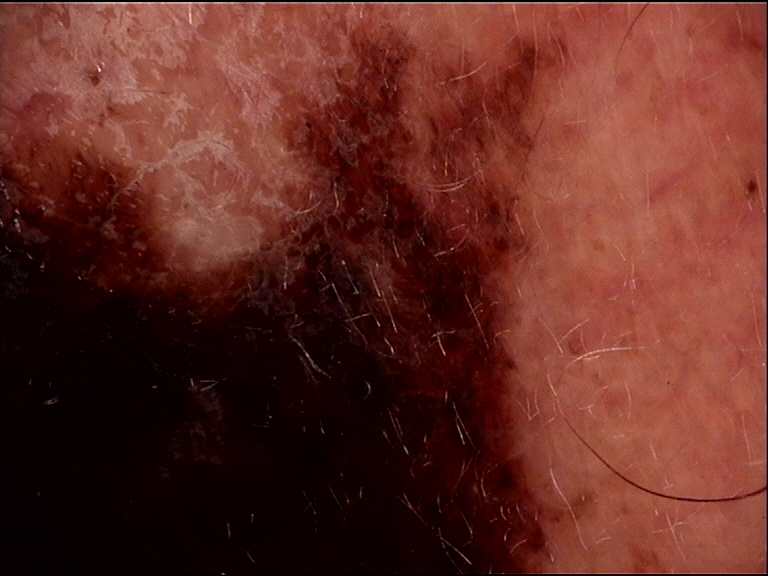| feature | finding |
|---|---|
| diagnostic label | melanoma (biopsy-proven) |